Fitzpatrick skin type II; human graders estimated a MST of 3. The photograph was taken at an angle — 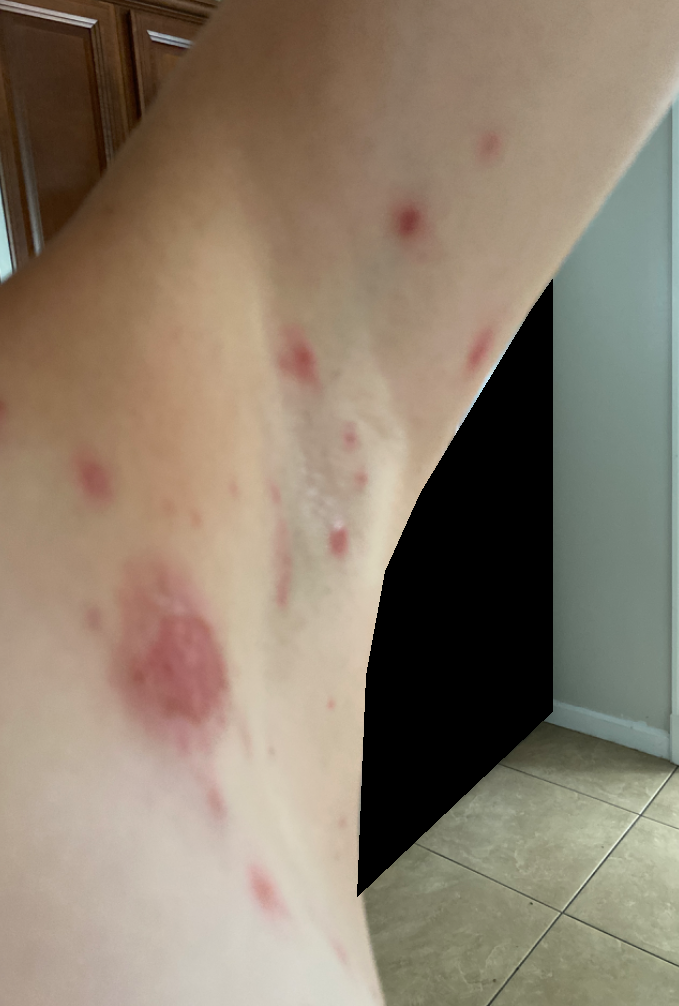Favoring Impetigo; the differential also includes Folliculitis.